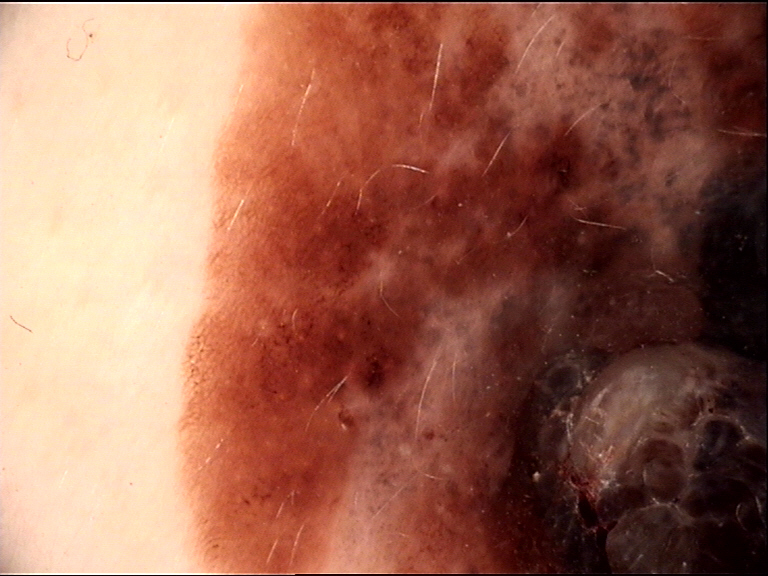pathology: melanoma (biopsy-proven).